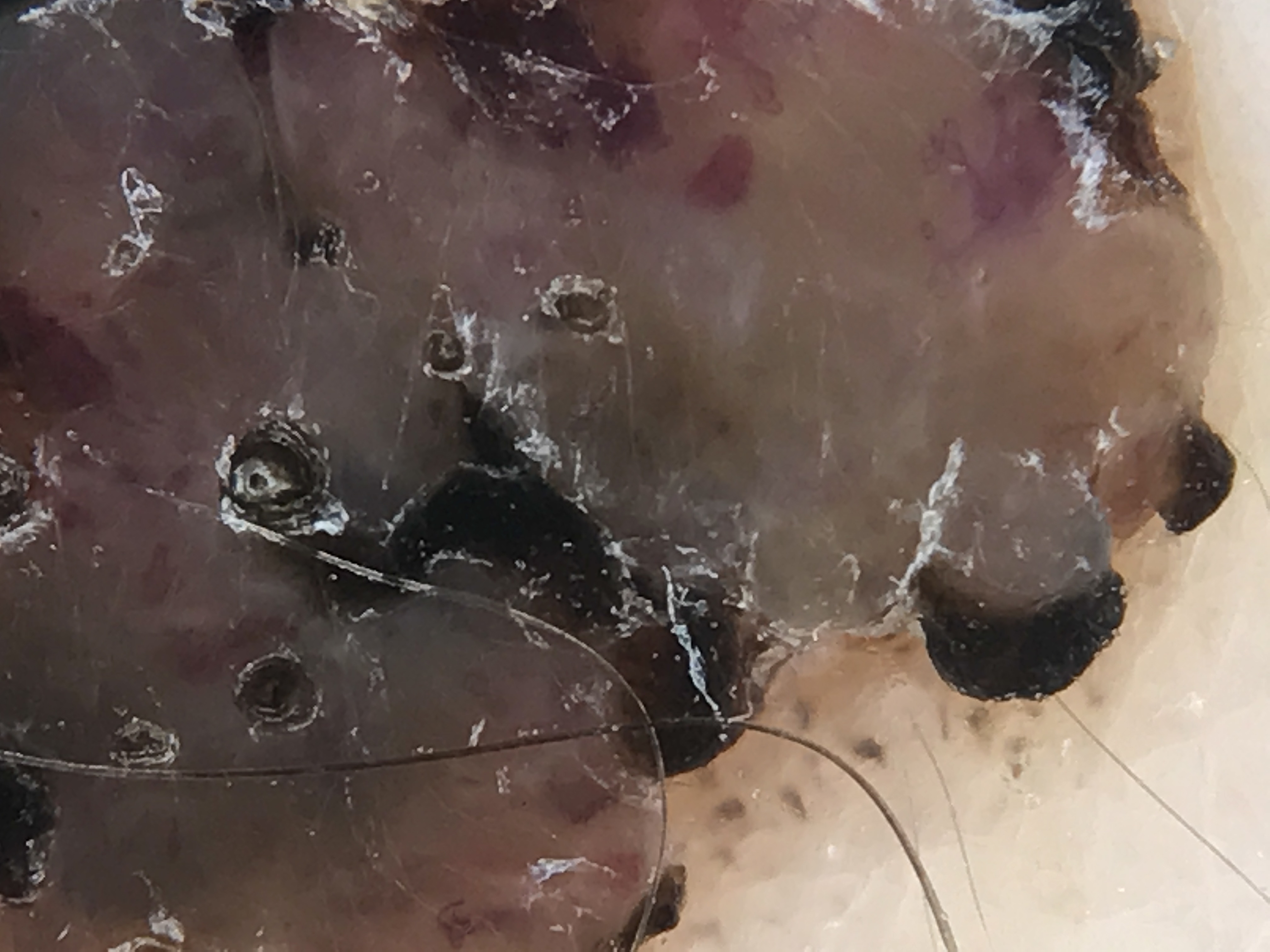A dermoscopic photograph of a skin lesion. Diagnosed as a benign lesion — a congenital dysplastic compound nevus.